A female patient aged 51. History notes prior skin cancer (patient or family). The patient was assessed as FST I. A clinical photo of a skin lesion taken with a smartphone.
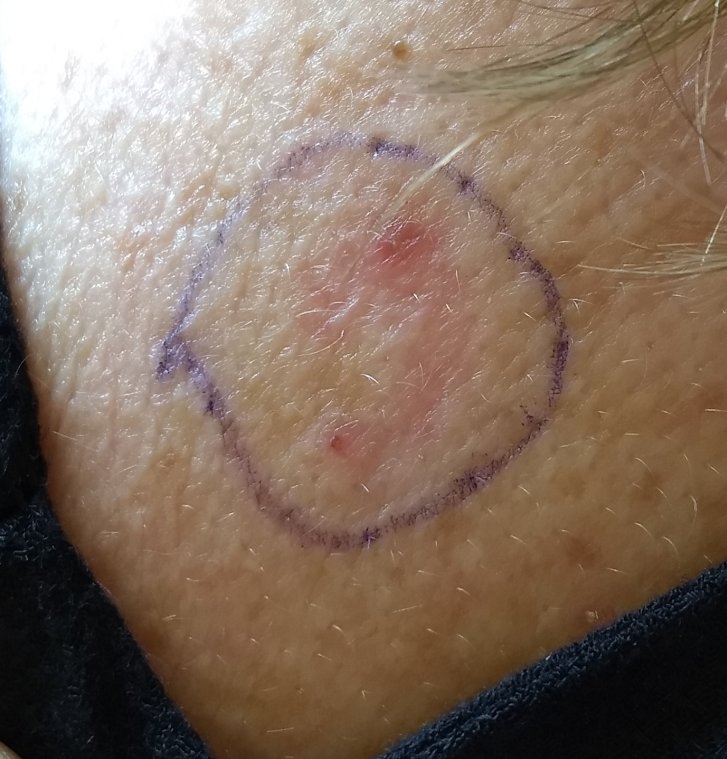site=the back; size=12x8 mm; patient-reported symptoms=no change in appearance; pathology=basal cell carcinoma (biopsy-proven).